A dermoscopic close-up of a skin lesion:
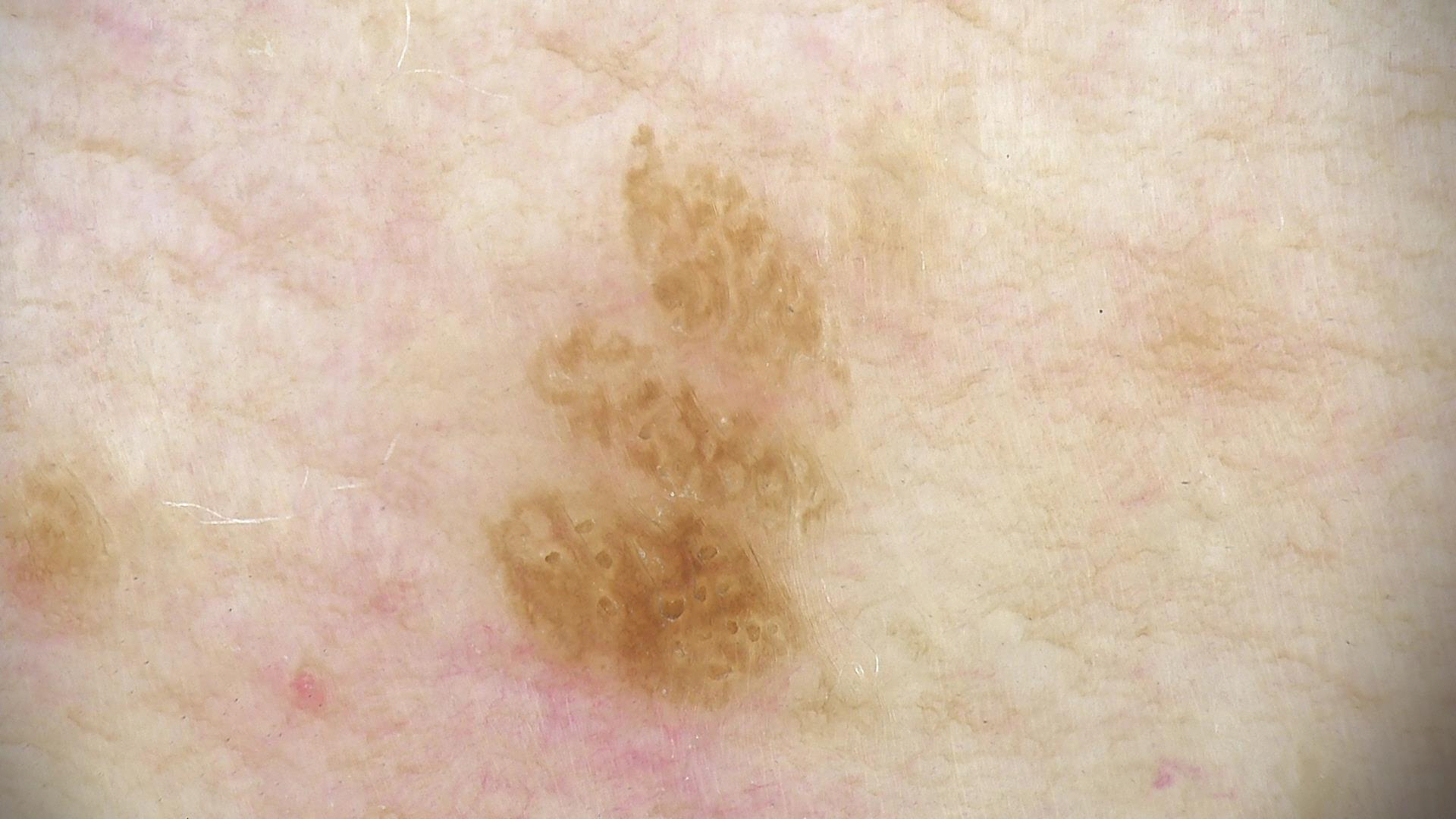category = keratinocytic | label = seborrheic keratosis (expert consensus).